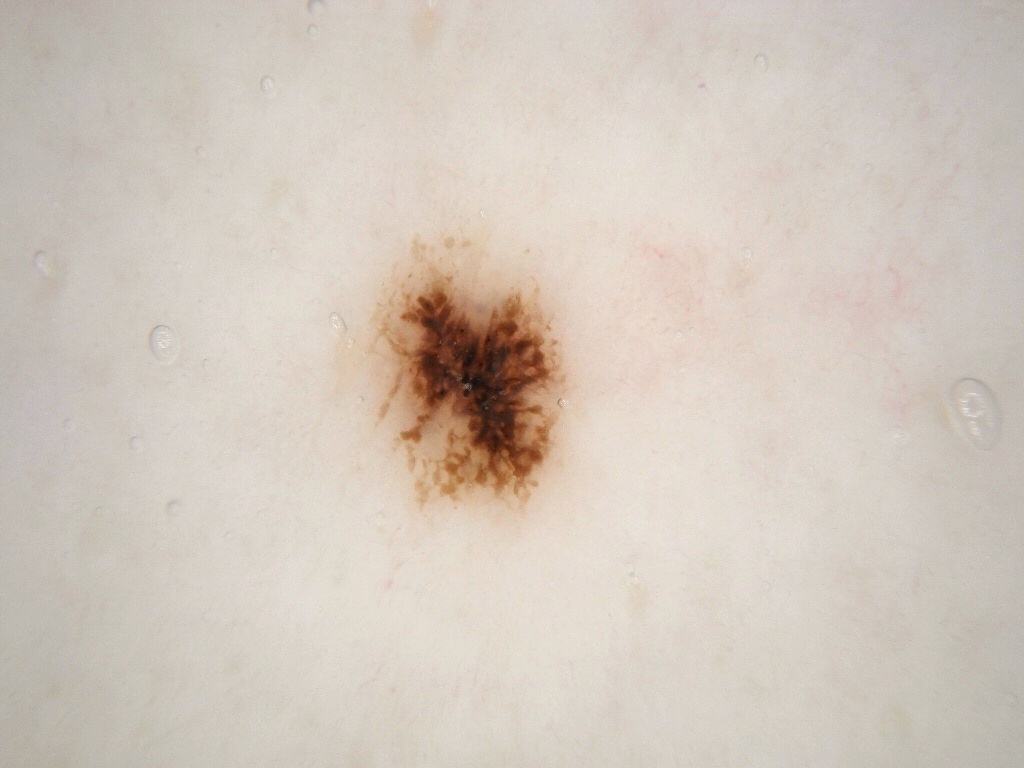| field | value |
|---|---|
| image type | dermatoscopic image of a skin lesion |
| lesion bbox | box(351, 225, 582, 540) |
| diagnostic label | a melanocytic nevus, a benign skin lesion |